Located on the leg · the photo was captured at an angle:
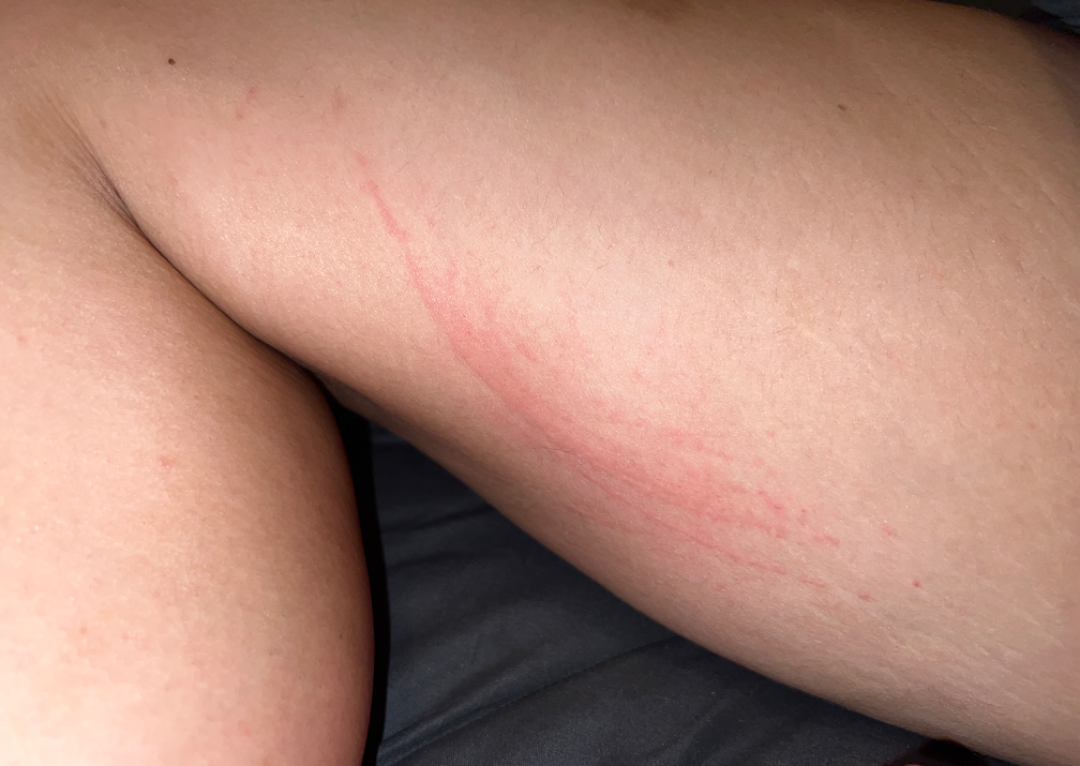Assessment: Diagnostic features were not clearly distinguishable in this photograph. Clinical context: Present for about one day. Texture is reported as raised or bumpy. The contributor reports burning and itching.